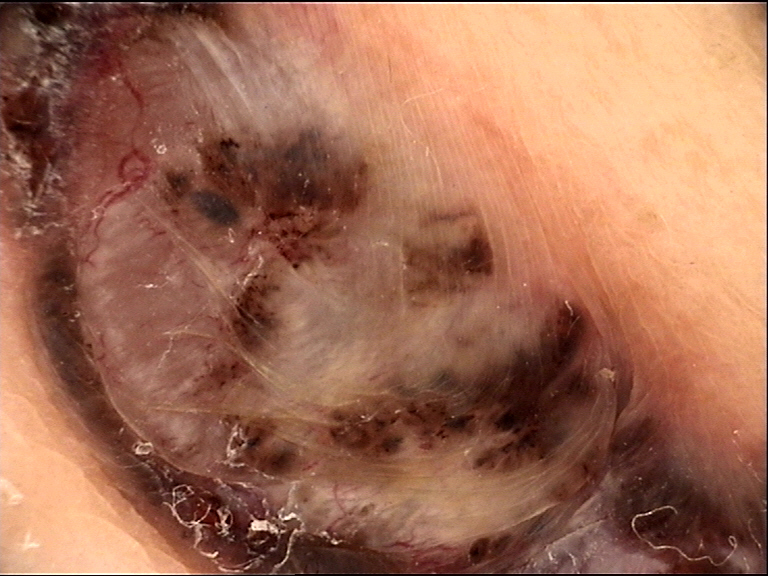Q: What kind of image is this?
A: dermoscopy
Q: What is the diagnosis?
A: basal cell carcinoma (biopsy-proven)